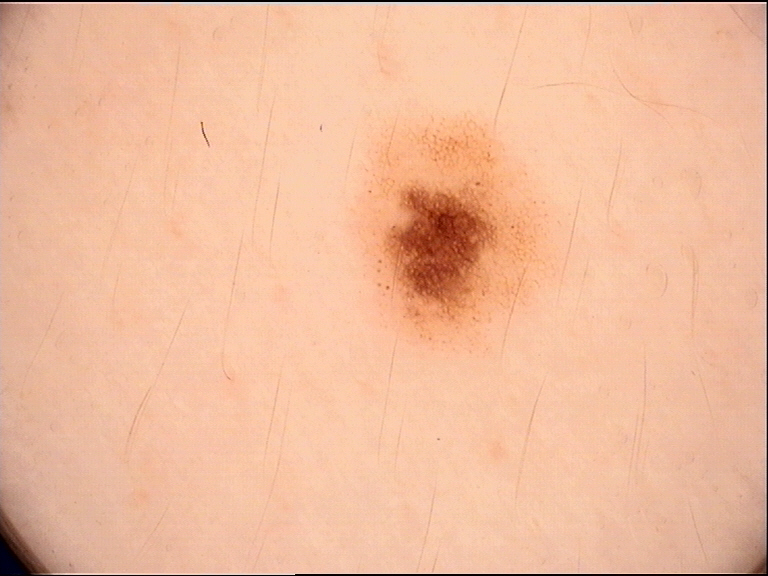A dermoscopic image of a skin lesion. Consistent with a dysplastic junctional nevus.